A skin lesion imaged with a dermatoscope.
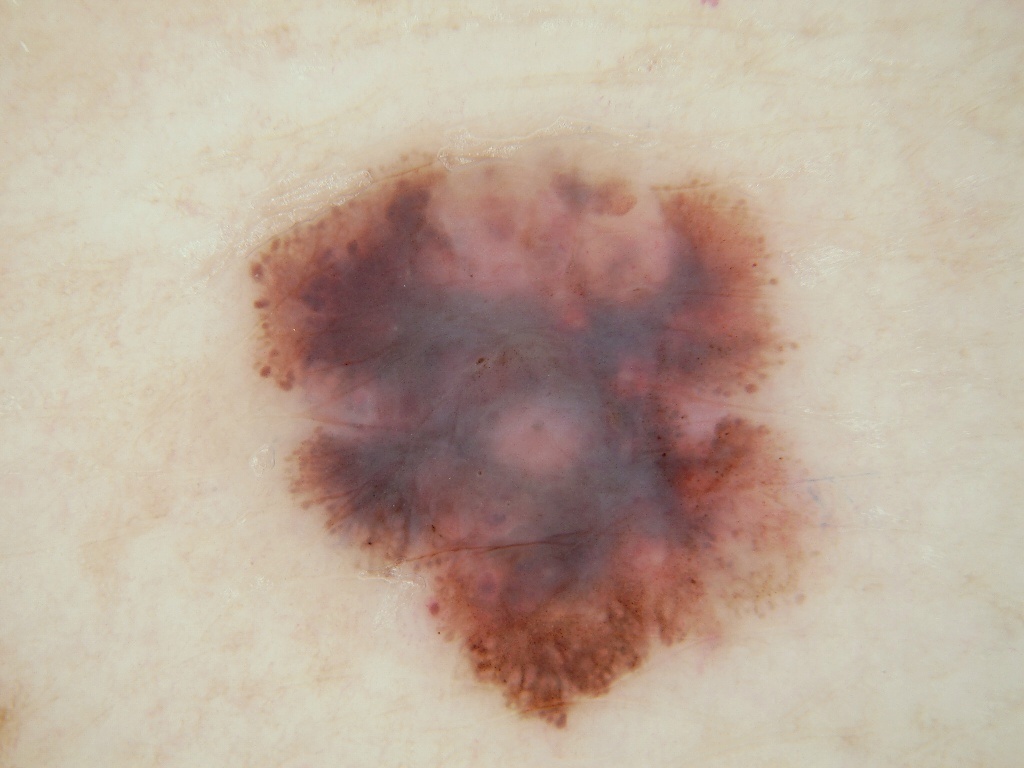Dermoscopically, the lesion shows streaks, globules, and pigment network. The lesion is located at left=239, top=129, right=838, bottom=737. Confirmed on histopathology as a melanoma, a malignant skin lesion.